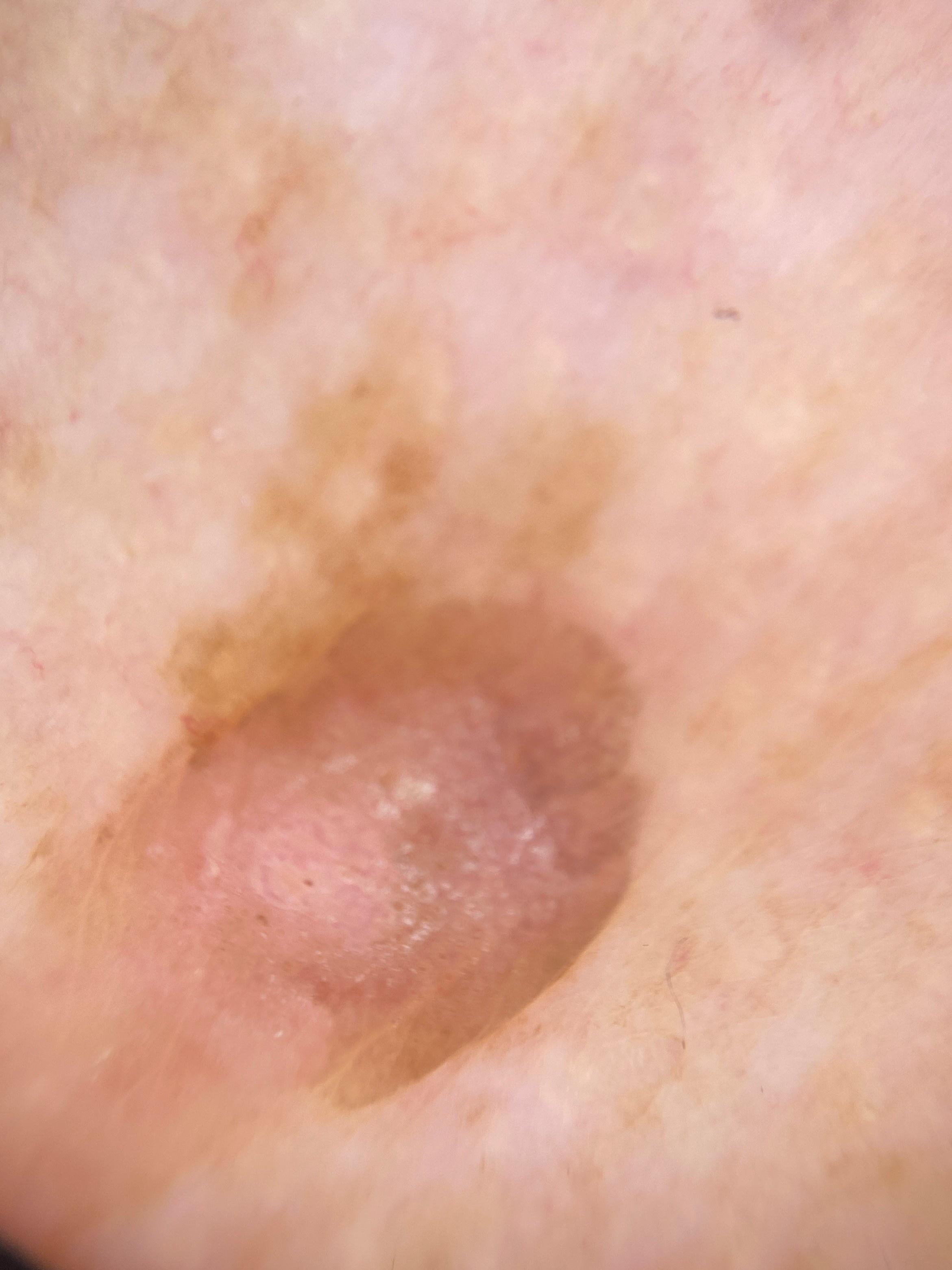{"image": "dermoscopic image", "patient": {"age_approx": 55, "sex": "female"}, "lesion_location": {"region": "the trunk", "detail": "the anterior trunk"}, "diagnosis": {"name": "Squamous cell carcinoma", "malignancy": "malignant", "confirmation": "histopathology", "lineage": "epidermal"}}